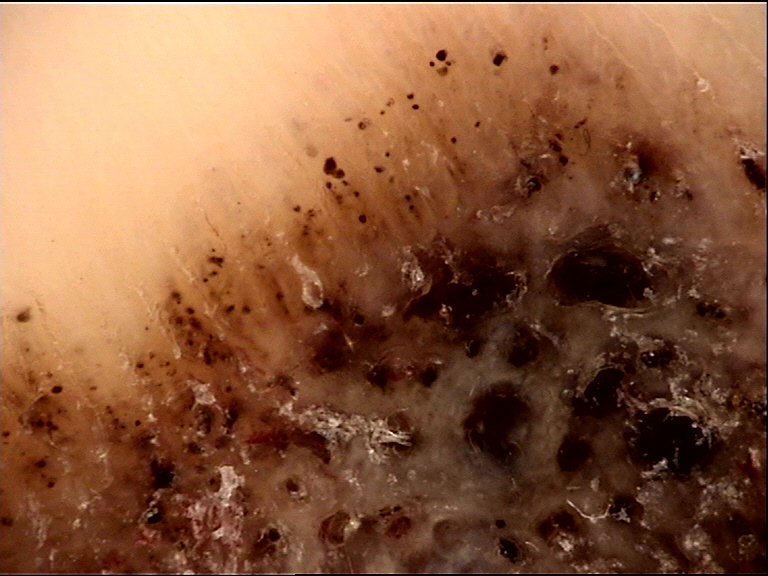| feature | finding |
|---|---|
| class | acral nodular melanoma (biopsy-proven) |